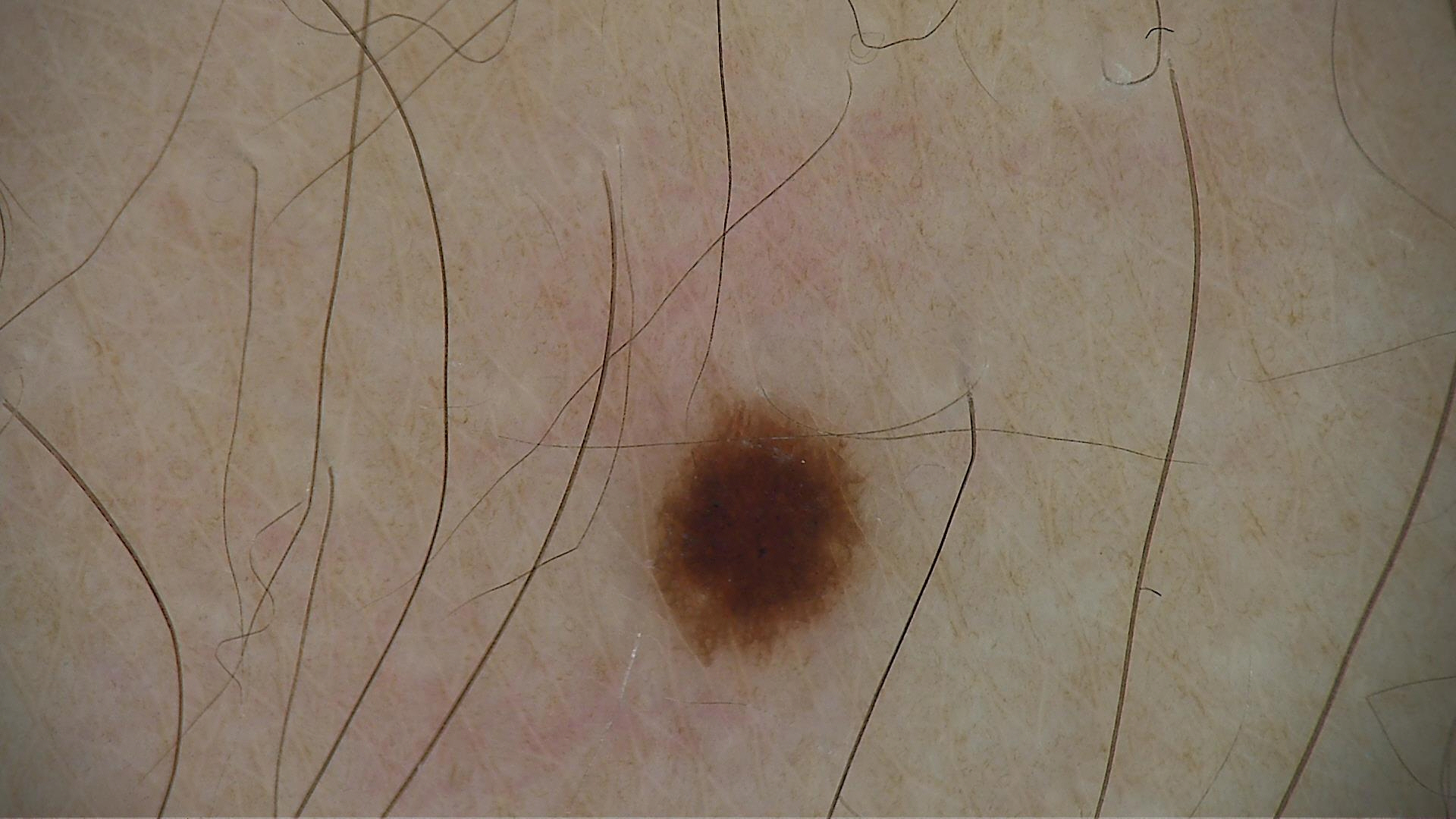Dermoscopy of a skin lesion. The morphology is that of a banal lesion. Labeled as a junctional nevus.